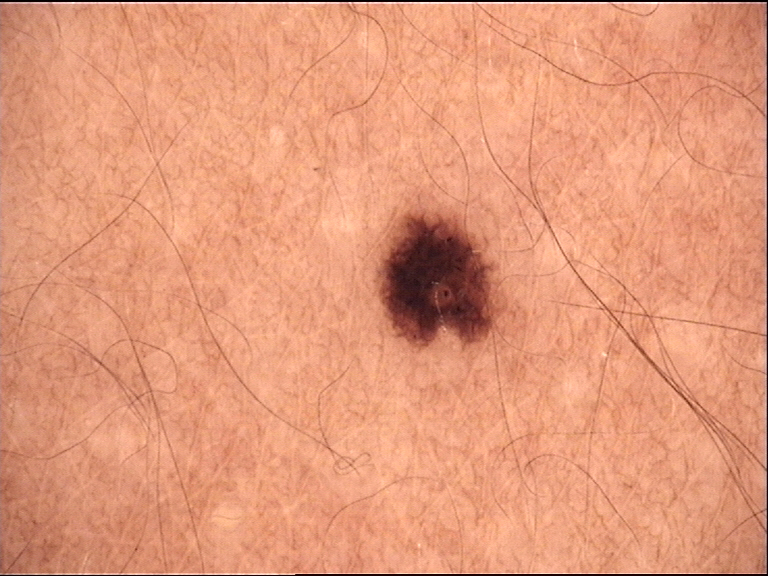image type=dermoscopy | category=banal | assessment=junctional nevus (expert consensus).